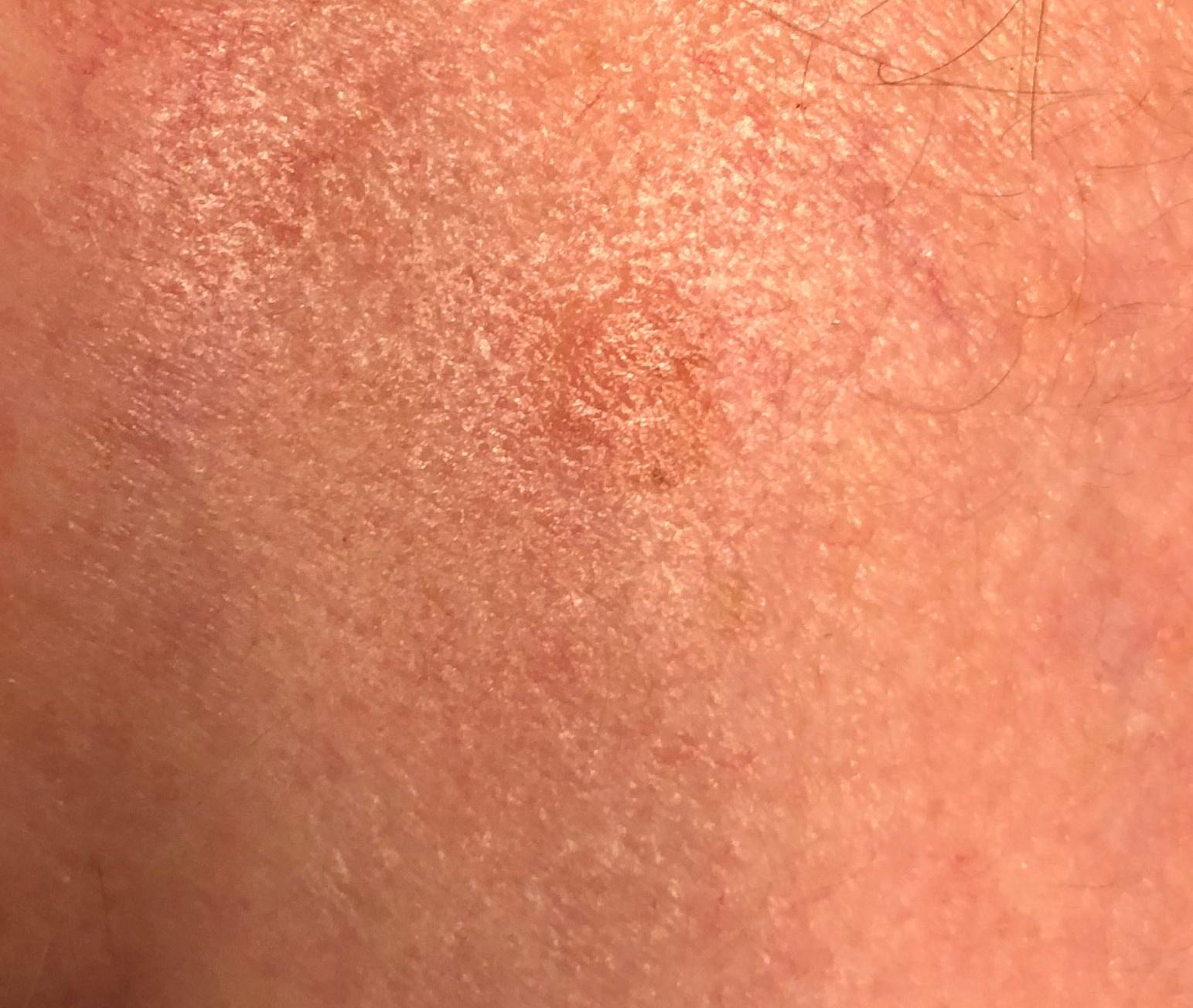Q: What is the diagnosis?
A: Seborrheic keratosis (biopsy-proven)